Dermoscopy of a skin lesion:
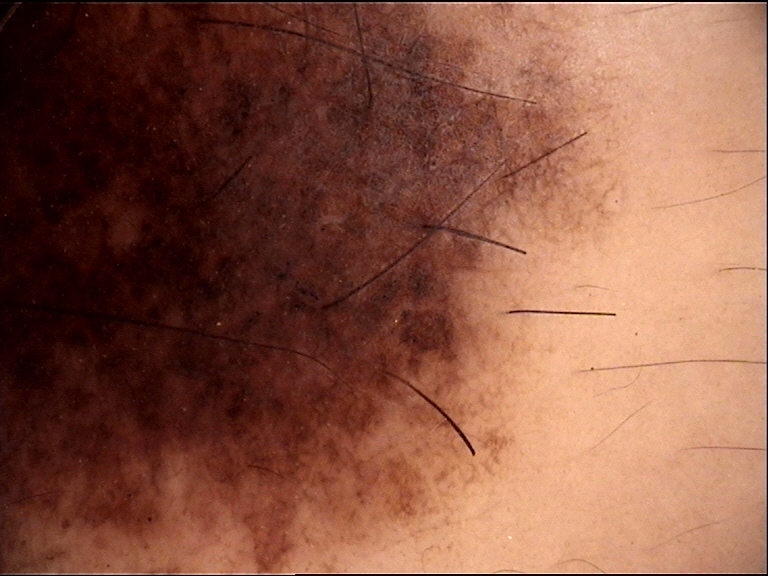Diagnosed as a congenital compound nevus.